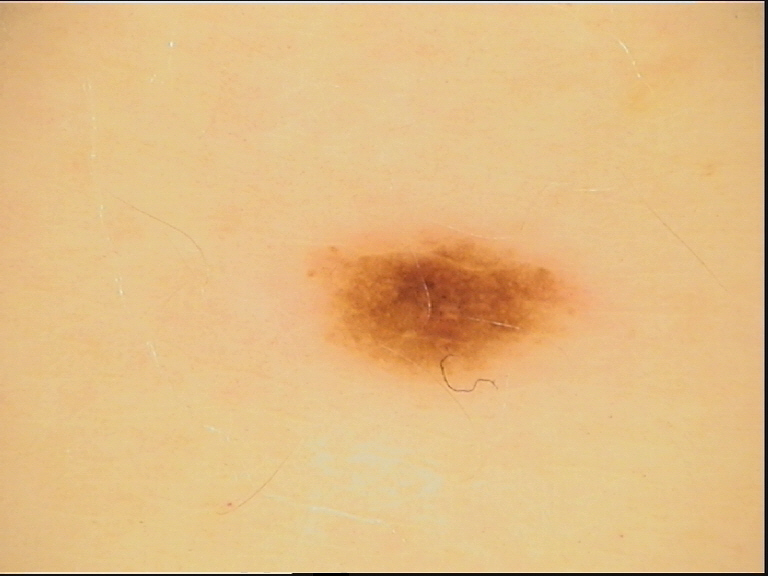Q: What kind of image is this?
A: dermatoscopy
Q: What is this lesion?
A: dysplastic junctional nevus (expert consensus)